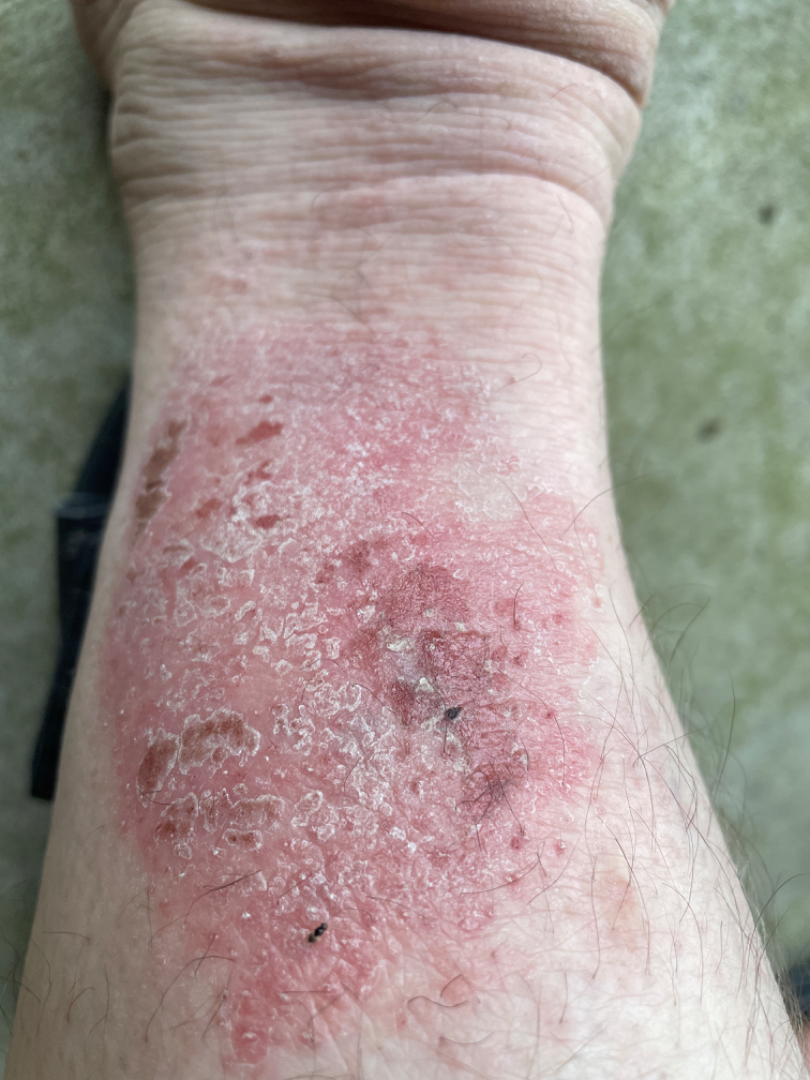{
  "differential": {
    "tied_lead": [
      "Eczema",
      "Impetigo",
      "Allergic Contact Dermatitis"
    ]
  }
}